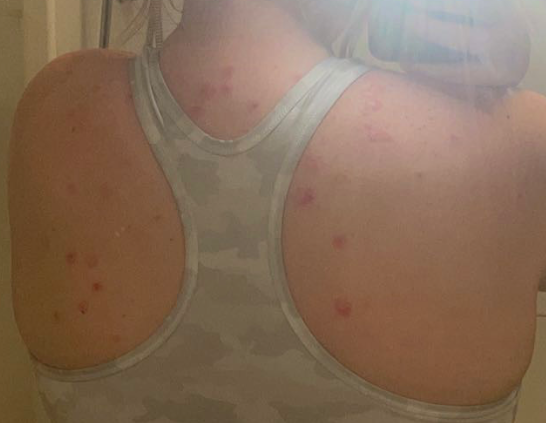Findings:
The skin findings could not be characterized from the image.
Background:
Reported duration is one to three months. The affected area is the arm, front of the torso, head or neck, leg and back of the torso. An image taken at a distance. The patient reports the lesion is raised or bumpy.